A dermoscopic close-up of a skin lesion.
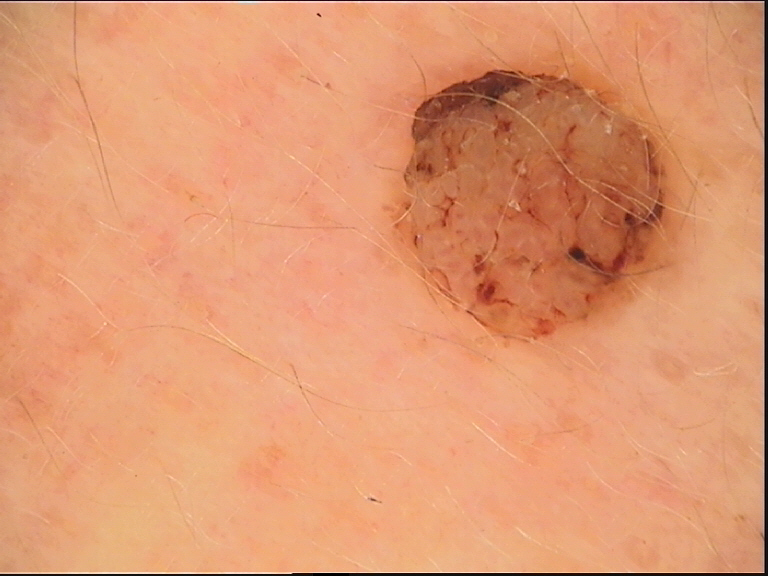Classified as a banal lesion — a dermal nevus.